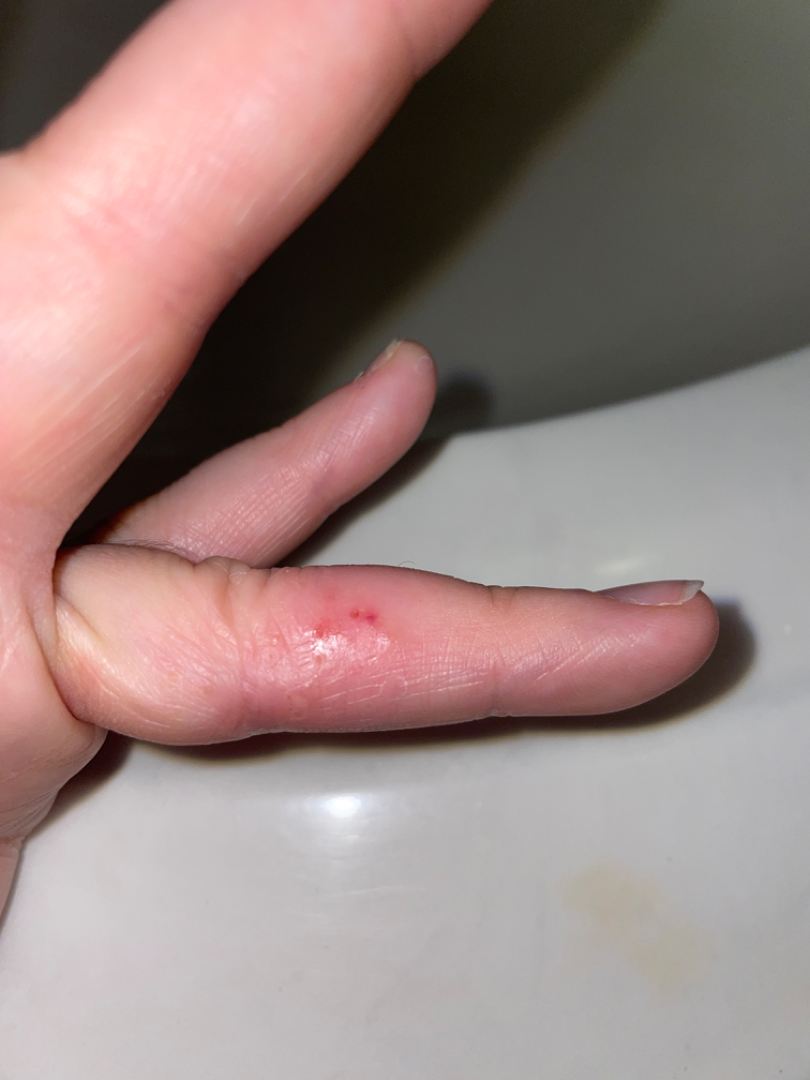The case was difficult to assess from the available photograph.
The subject is a female aged 30–39.
This is a close-up image.